No associated systemic symptoms reported, reported lesion symptoms include itching, the lesion is described as rough or flaky and raised or bumpy, present for more than one year, the affected area is the leg, the patient considered this a rash, the patient is a female aged 30–39, close-up view, skin tone: Fitzpatrick II; lay reviewers estimated a Monk Skin Tone of 1: 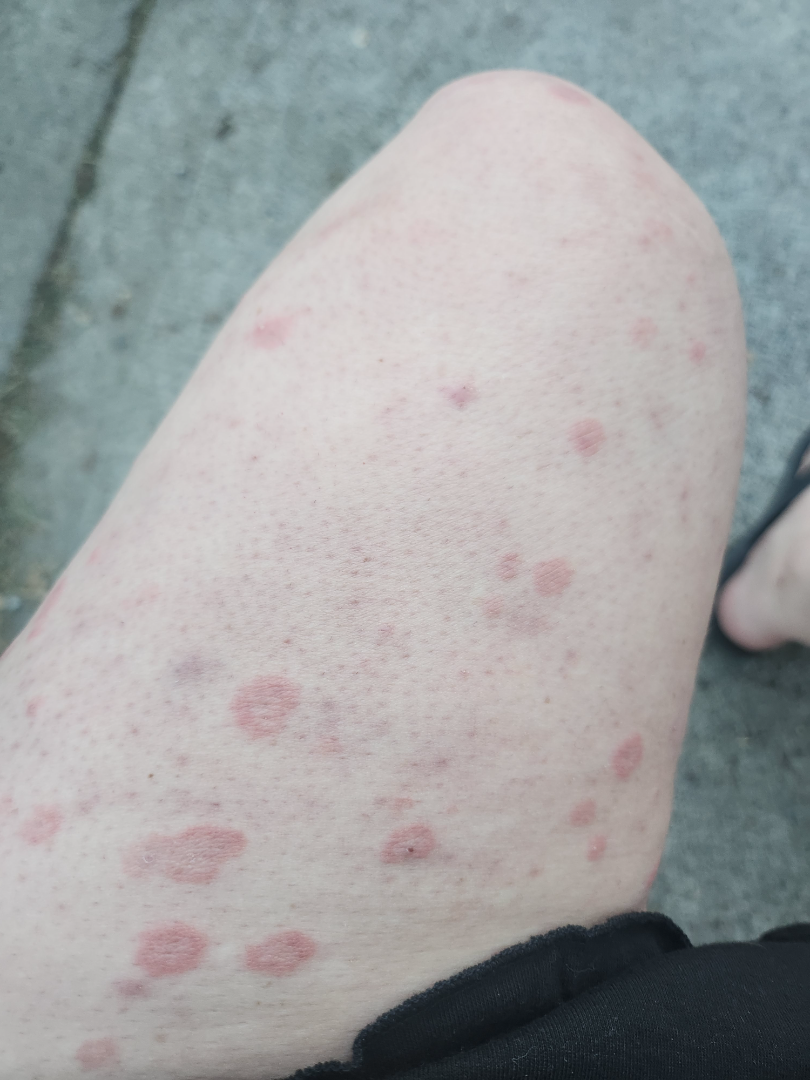  differential: Psoriasis